The photo was captured at an angle:
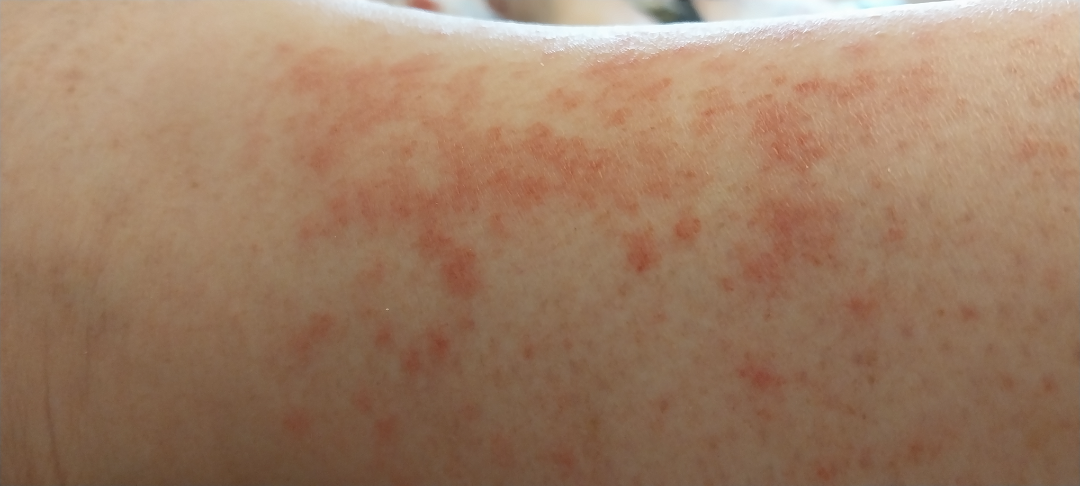assessment: unable to determine